A dermoscopic photograph of a skin lesion: 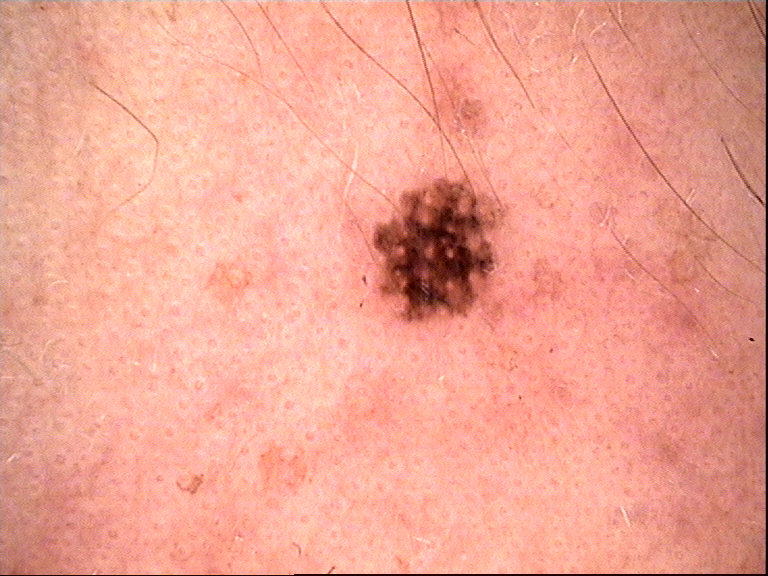Consistent with a compound lesion — a Miescher nevus.